An image taken at a distance; the patient is male: 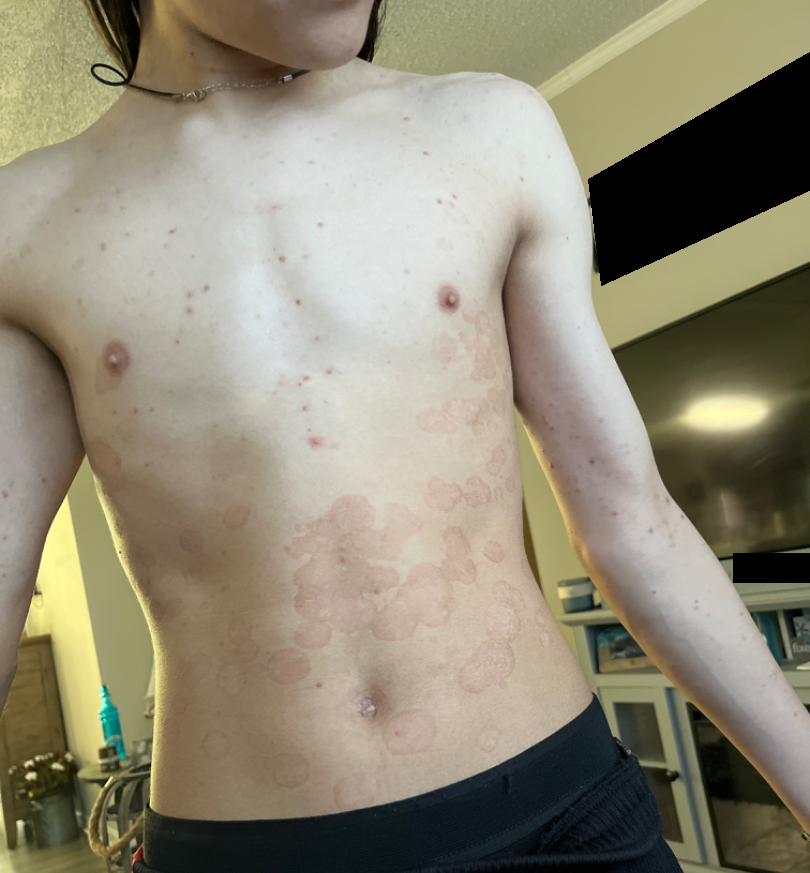clinical impression = the leading consideration is Psoriasis; the differential also includes Eczema; also consider Tinea Versicolor